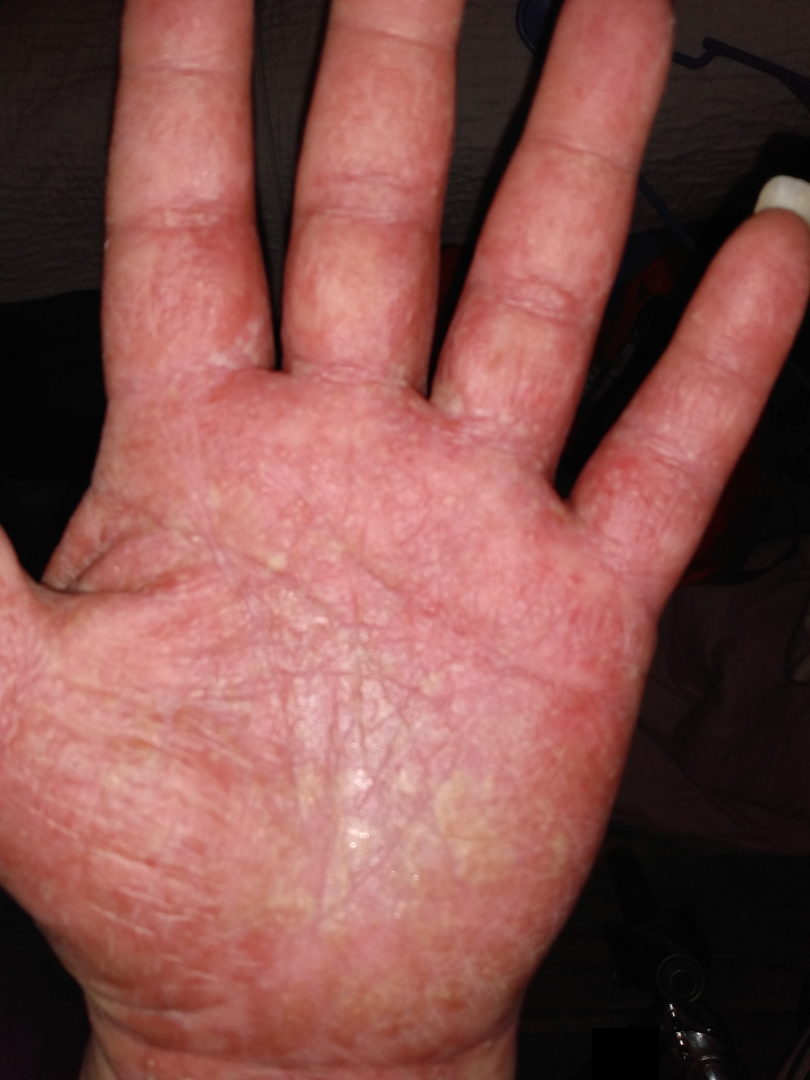Findings:
The reviewing dermatologist was unable to assign a differential diagnosis from the image.
Background:
An image taken at an angle. Skin tone: lay reviewers estimated MST 4 (US pool) or 3 (India pool).